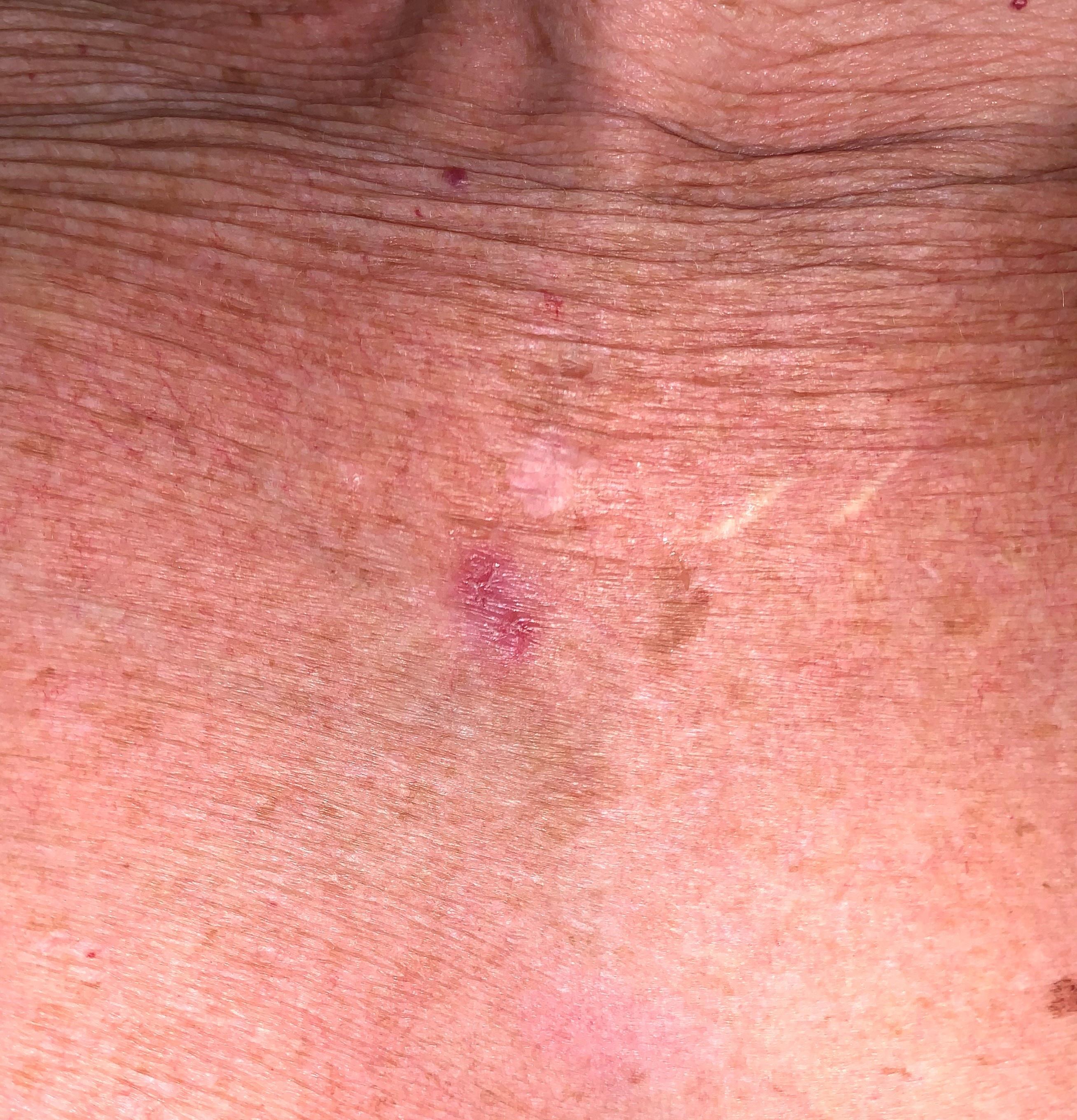Findings: Recorded as skin type II. A clinical photograph of a skin lesion. Located on the trunk (the anterior trunk). Conclusion: On biopsy, the diagnosis was a basal cell carcinoma.